Dermoscopy of a skin lesion.
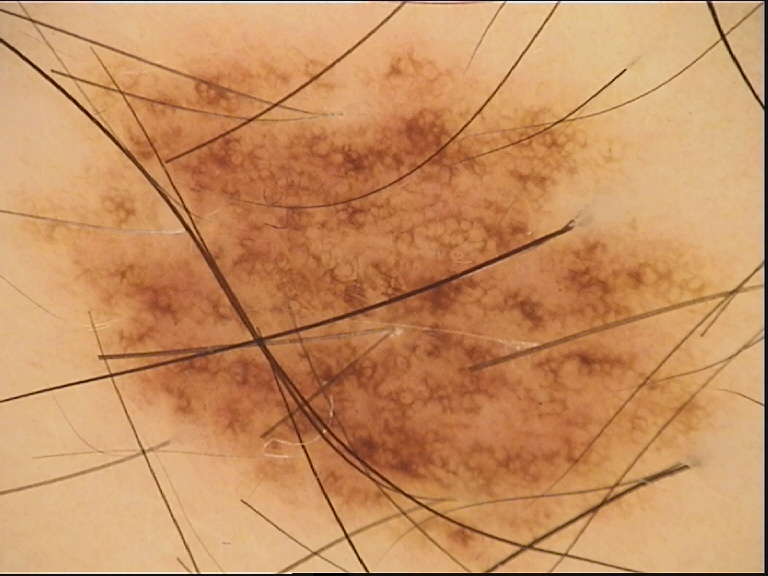{
  "diagnosis": {
    "name": "dysplastic junctional nevus",
    "code": "jd",
    "malignancy": "benign",
    "super_class": "melanocytic",
    "confirmation": "expert consensus"
  }
}